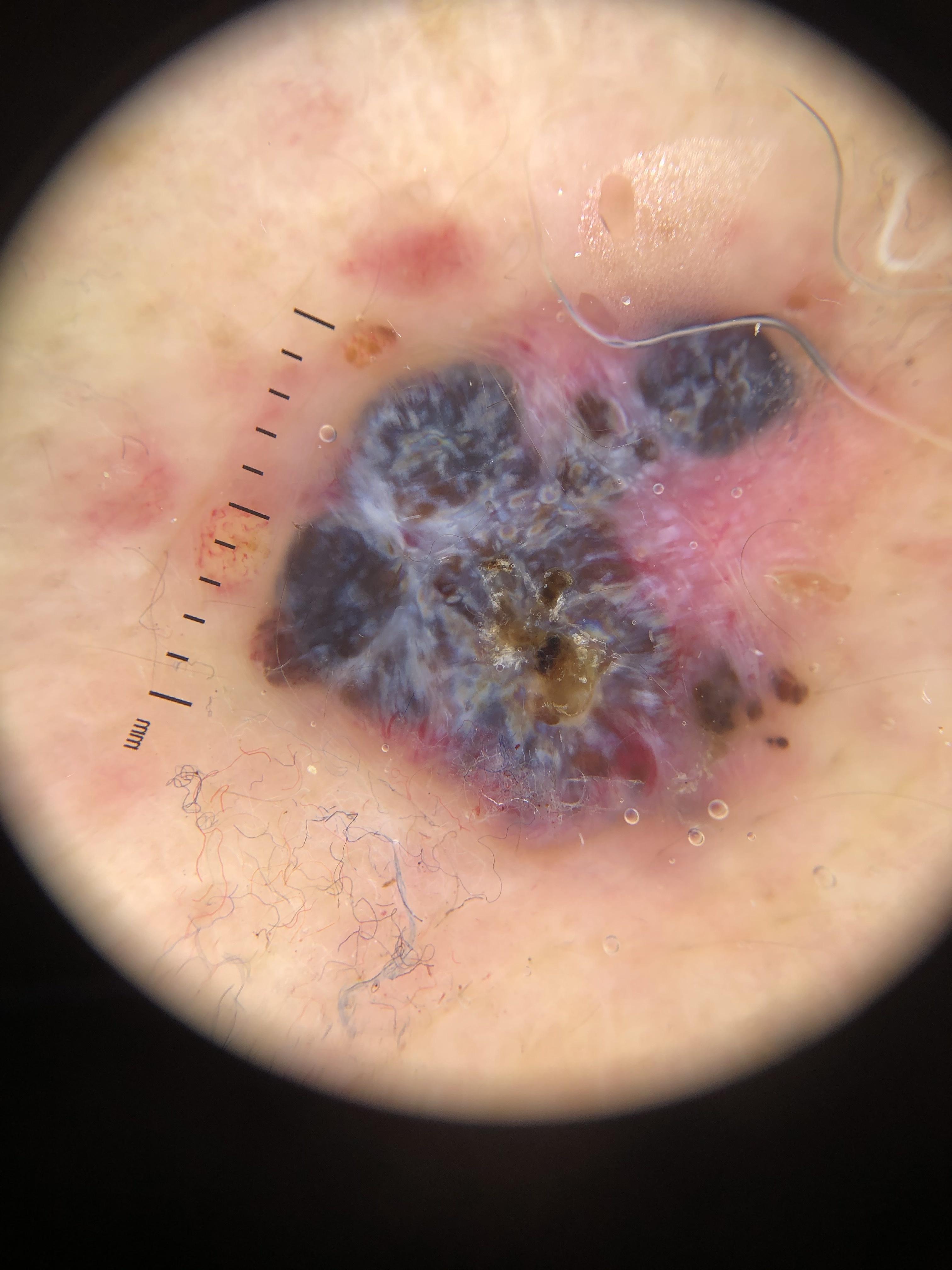image type — dermoscopic image
site — the trunk
diagnostic label — Melanoma (biopsy-proven)